A female subject in their mid- to late 70s; a skin lesion imaged with contact-polarized dermoscopy; per the chart, a prior melanoma but no melanoma in first-degree relatives; the patient is Fitzpatrick phototype II: 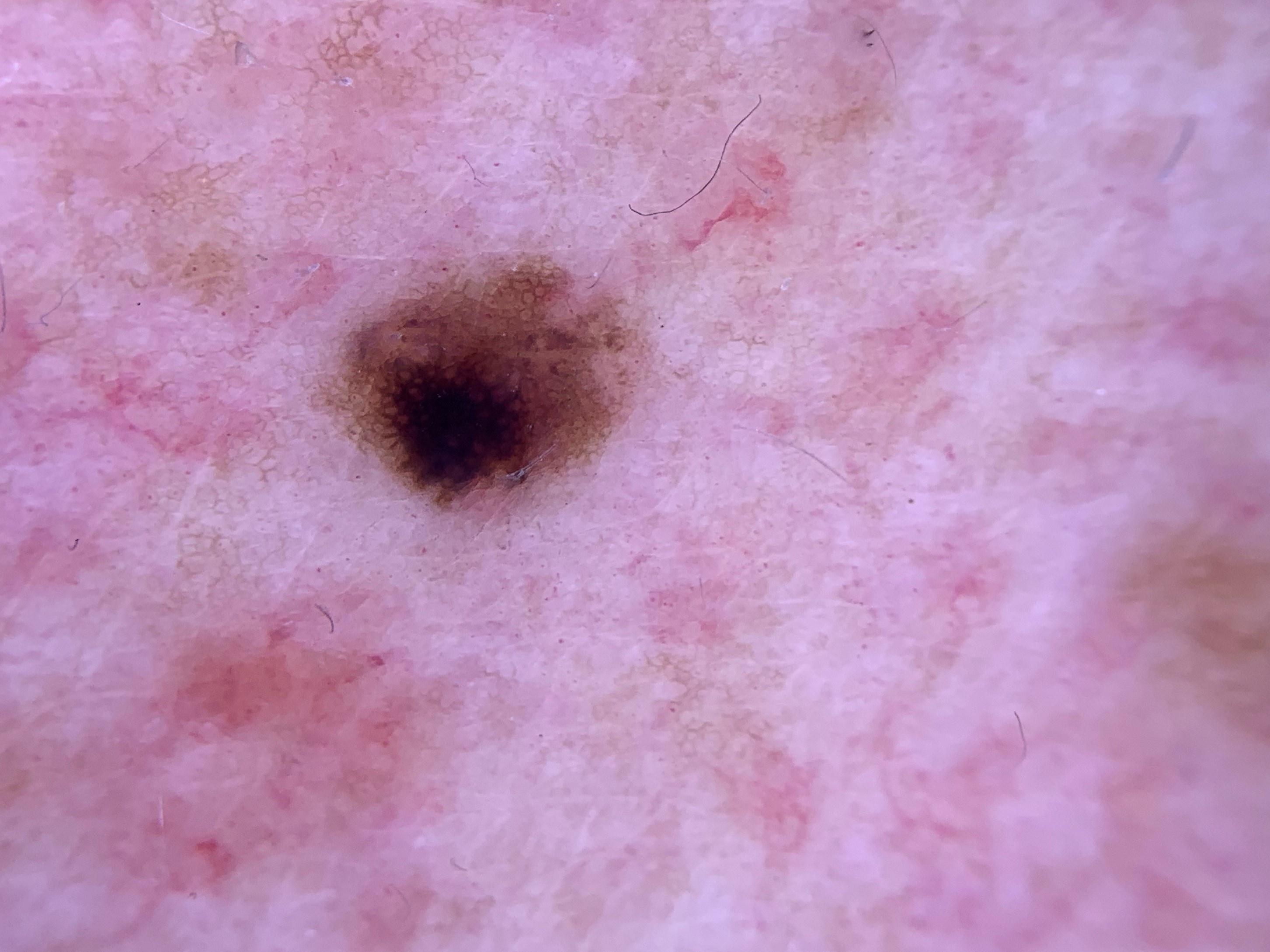The lesion is located on the posterior trunk. Biopsy-confirmed as a nevus.